Dermoscopy of a skin lesion.
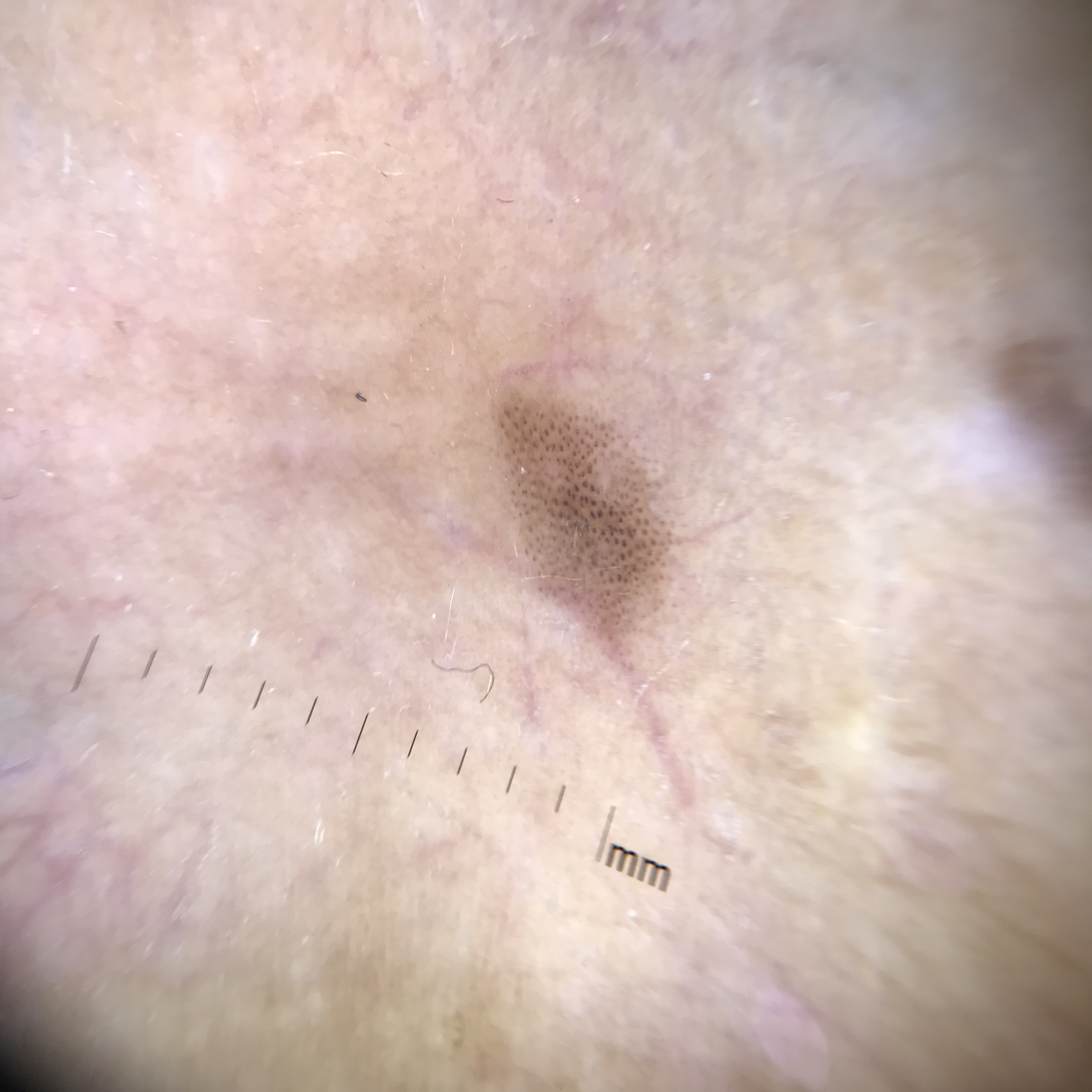Classified as a junctional nevus.